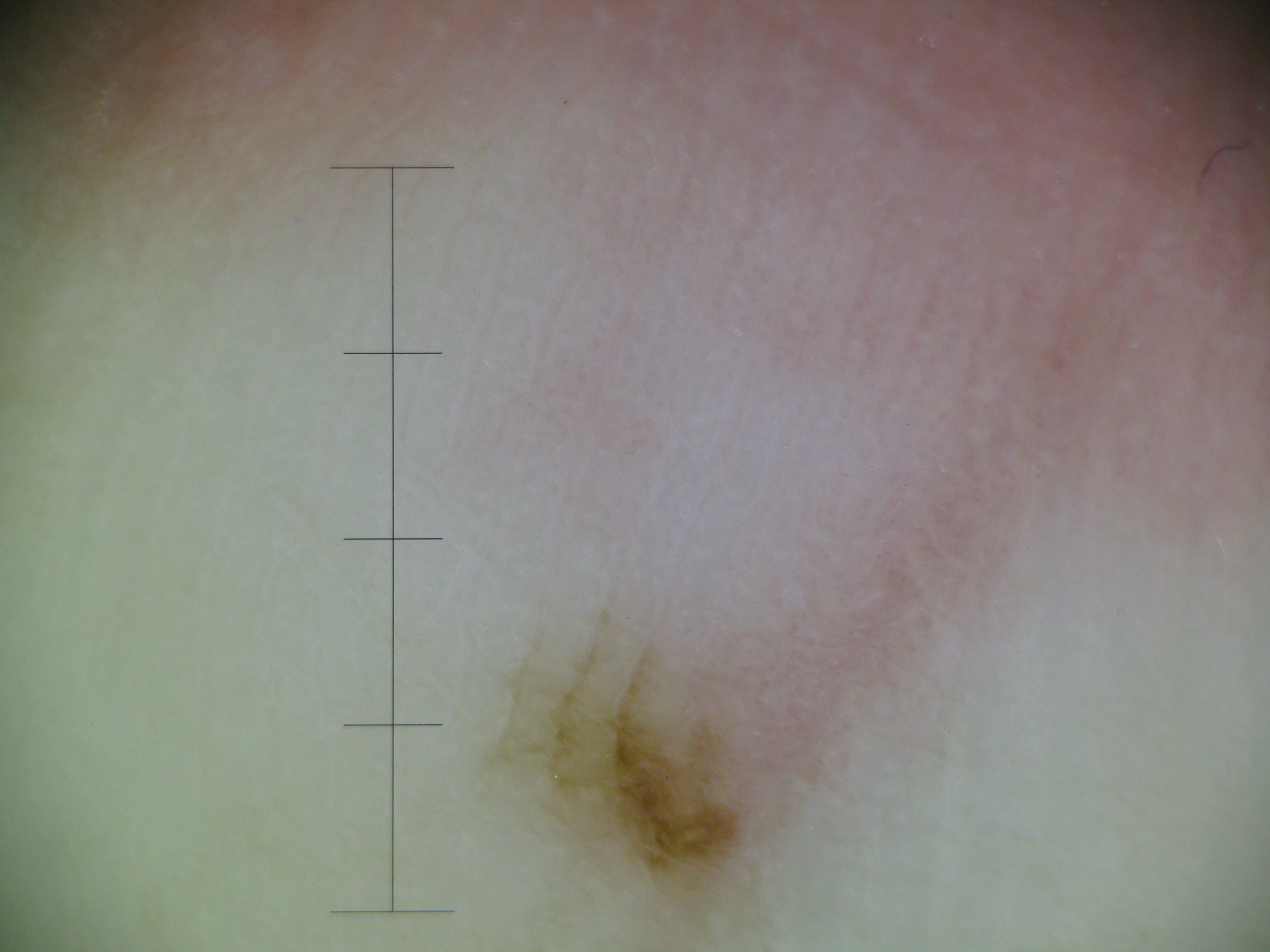  lesion_type:
    main_class: banal
    pattern: junctional
  diagnosis:
    name: acral junctional nevus
    code: ajb
    malignancy: benign
    super_class: melanocytic
    confirmation: expert consensus